A dermoscopic photograph of a skin lesion: 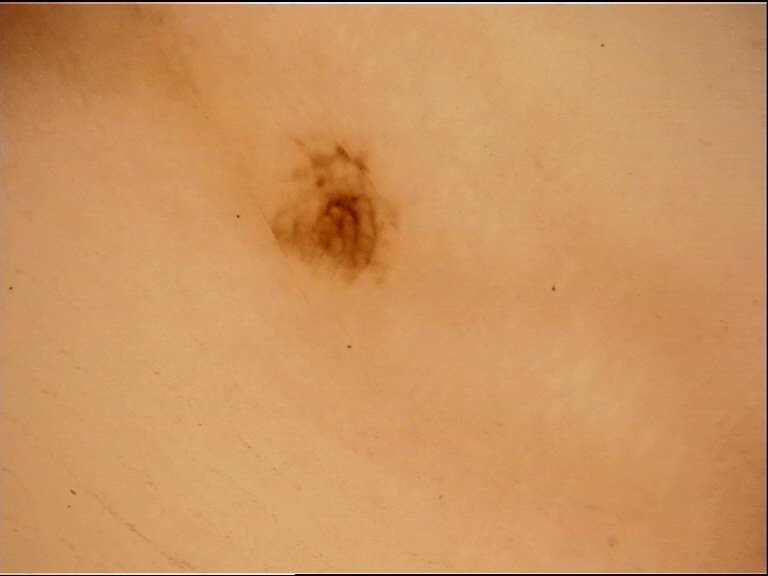– diagnostic label: acral dysplastic junctional nevus (expert consensus)